A dermatoscopic image of a skin lesion:
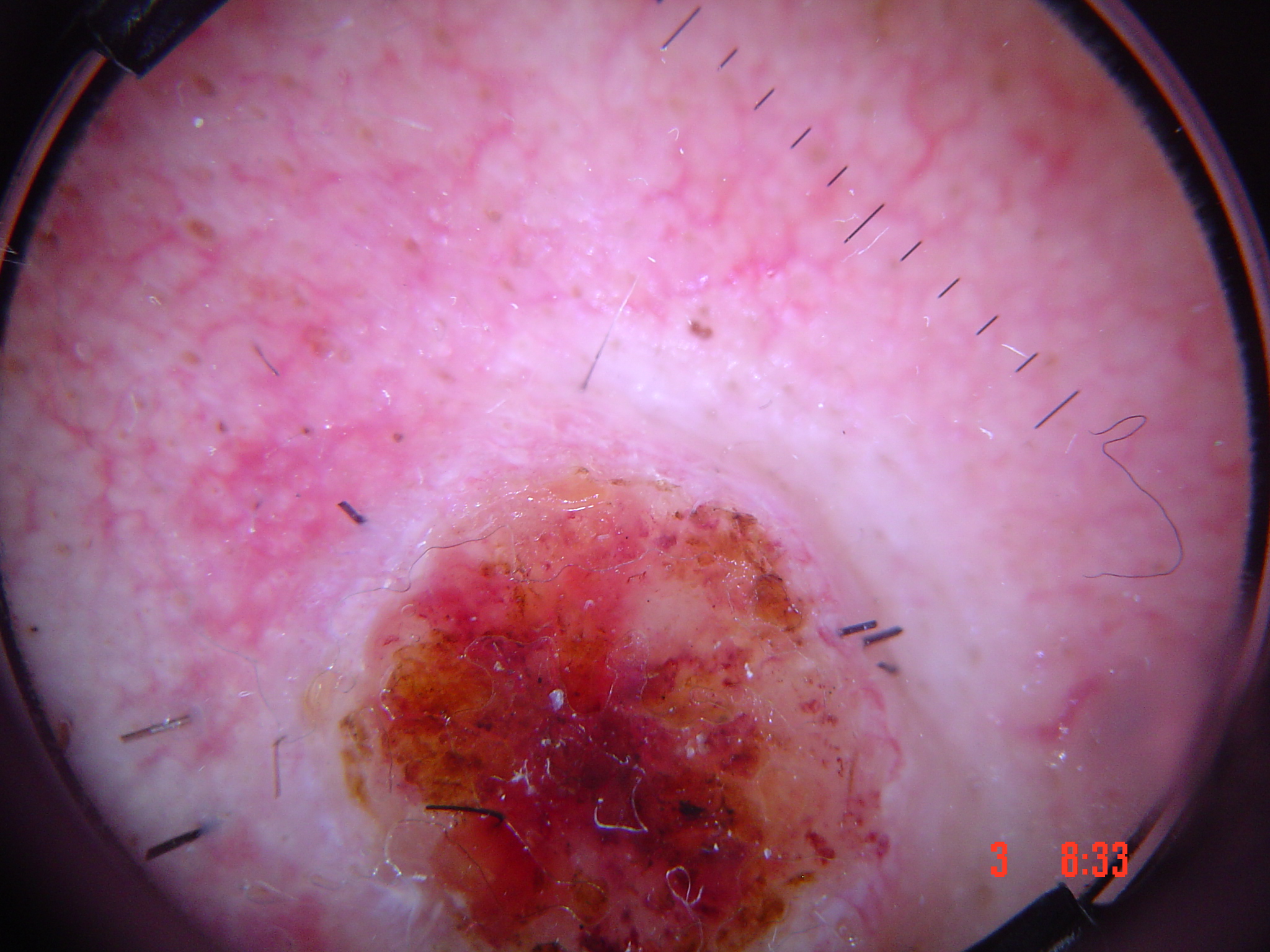Findings: This is a keratinocytic lesion. Diagnosis: Confirmed on histopathology as a malignant lesion — a squamous cell carcinoma.